The subject is 50–59, male; the photograph is a close-up of the affected area — 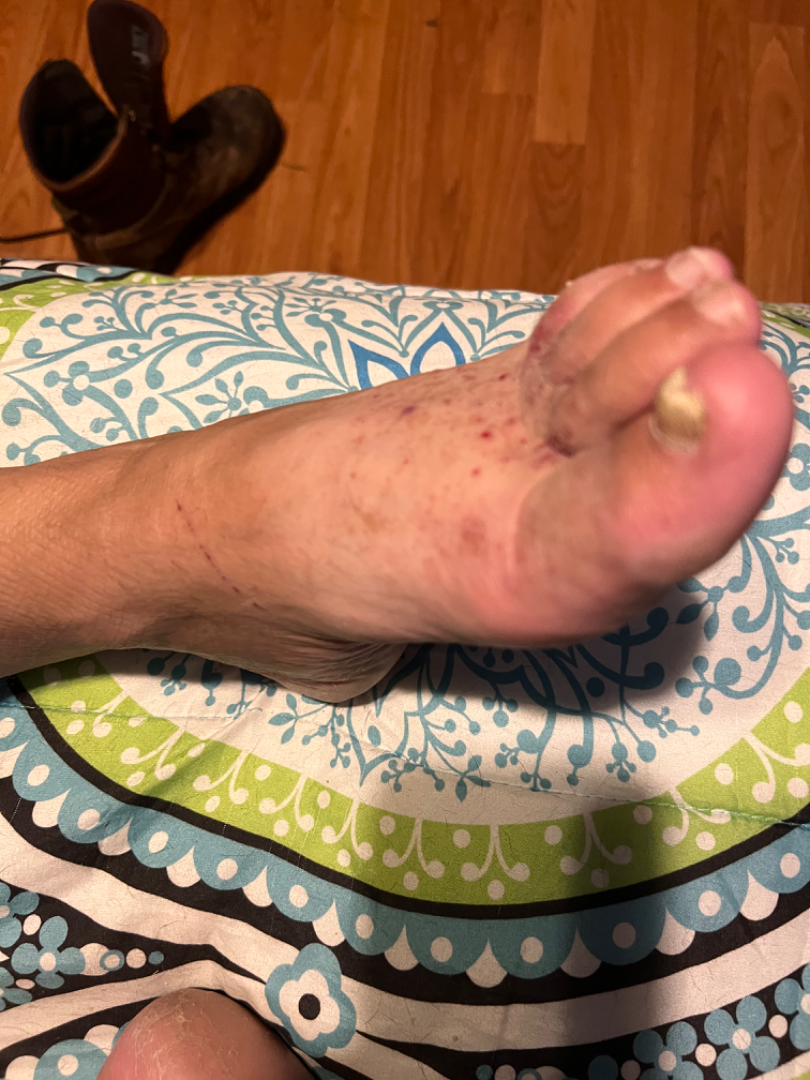Impression:
The case was difficult to assess from the available photograph.
History:
The patient notes the lesion is rough or flaky. No relevant systemic symptoms. The lesion is associated with itching, burning and bleeding. Reported duration is one to four weeks.